The lesion involves the head or neck · an image taken at an angle — 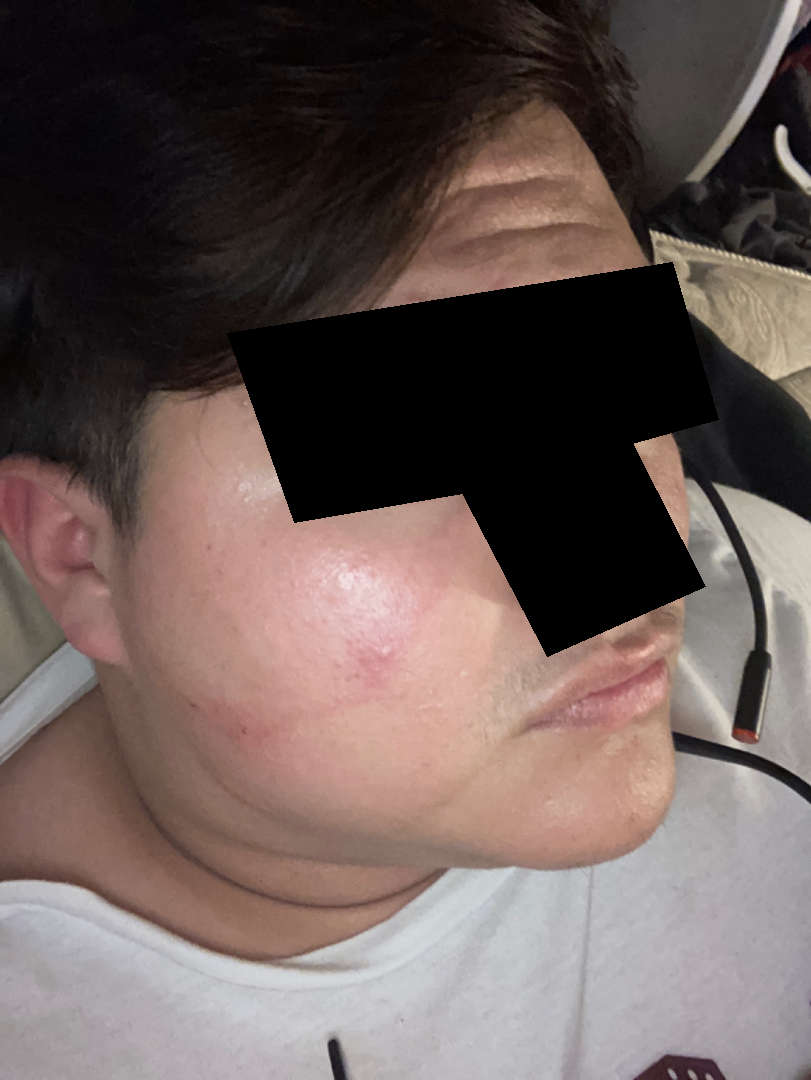texture = rough or flaky, impression = the leading consideration is Acne; also consider Irritant Contact Dermatitis.